The patient considered this a rash · present for about one day · skin tone: Fitzpatrick skin type II; non-clinician graders estimated Monk skin tone scale 2 · no relevant systemic symptoms · the contributor is female · the photograph was taken at a distance · reported lesion symptoms include burning, itching and bothersome appearance · texture is reported as flat · the lesion involves the front of the torso, head or neck and arm: 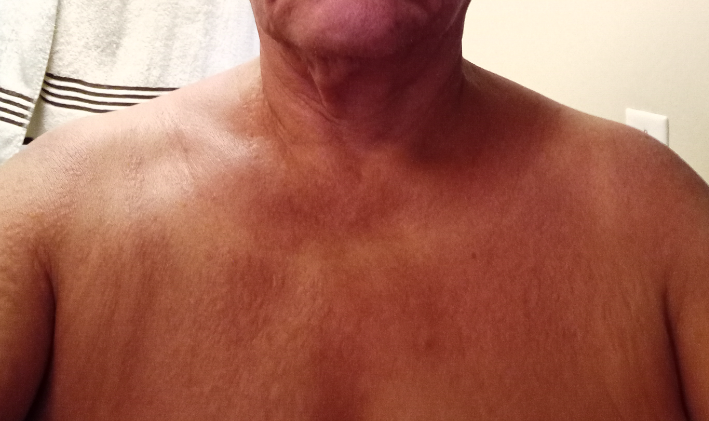On independent review by the dermatologists: Photodermatitis and Vitiligo were considered with similar weight.